The chart records pesticide exposure and no prior malignancy (patient or family) · a clinical photograph showing a skin lesion · the patient was assessed as skin type II: 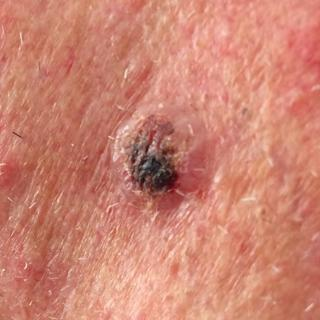region=the face
size=approx. 10 × 10 mm
reported symptoms=growth, elevation, itching, bleeding
diagnosis=basal cell carcinoma (biopsy-proven)